Close-up view — 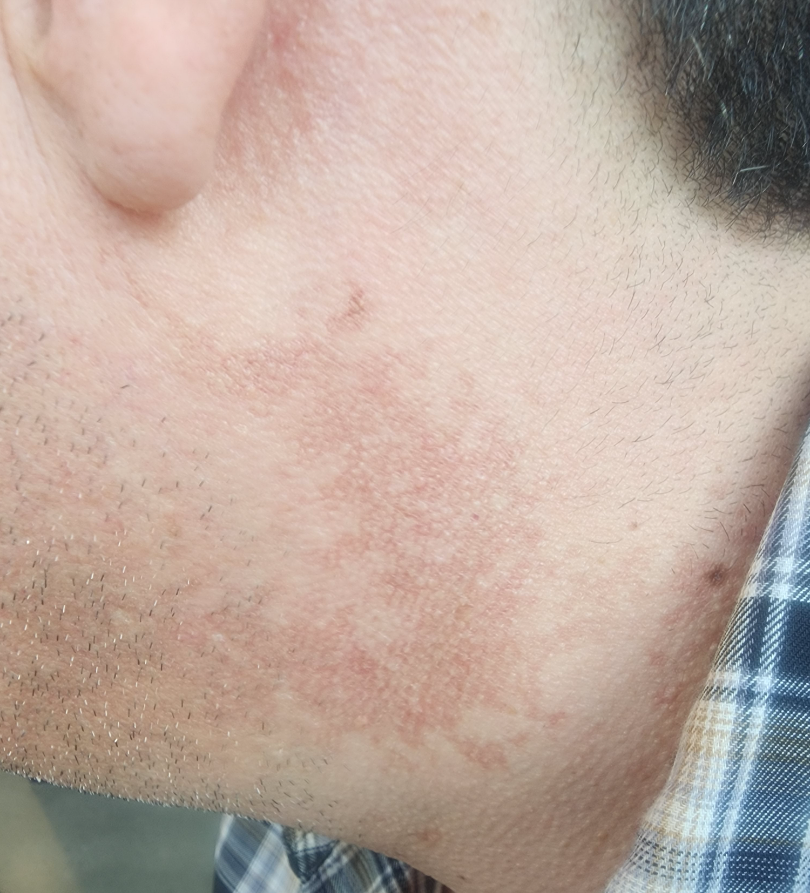differential — Poikiloderma (leading); Post-Inflammatory hyperpigmentation (considered).